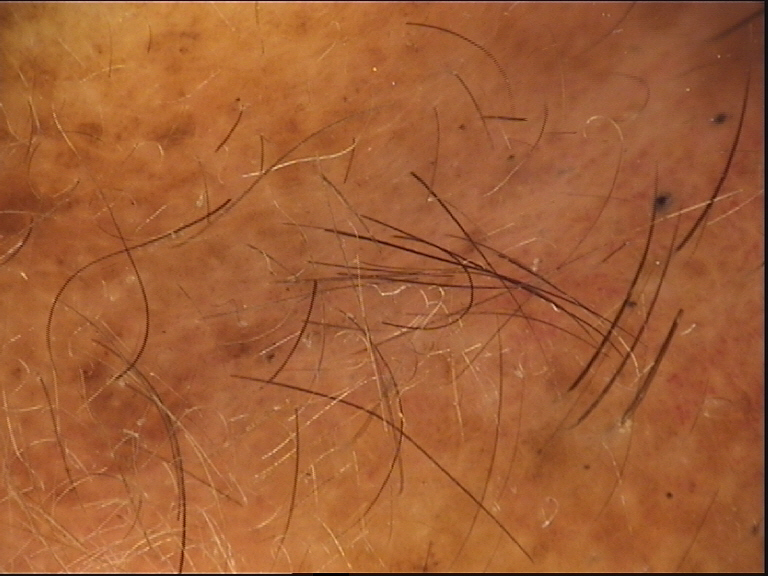A dermoscopic close-up of a skin lesion. The diagnostic label was a banal lesion — a congenital compound nevus.